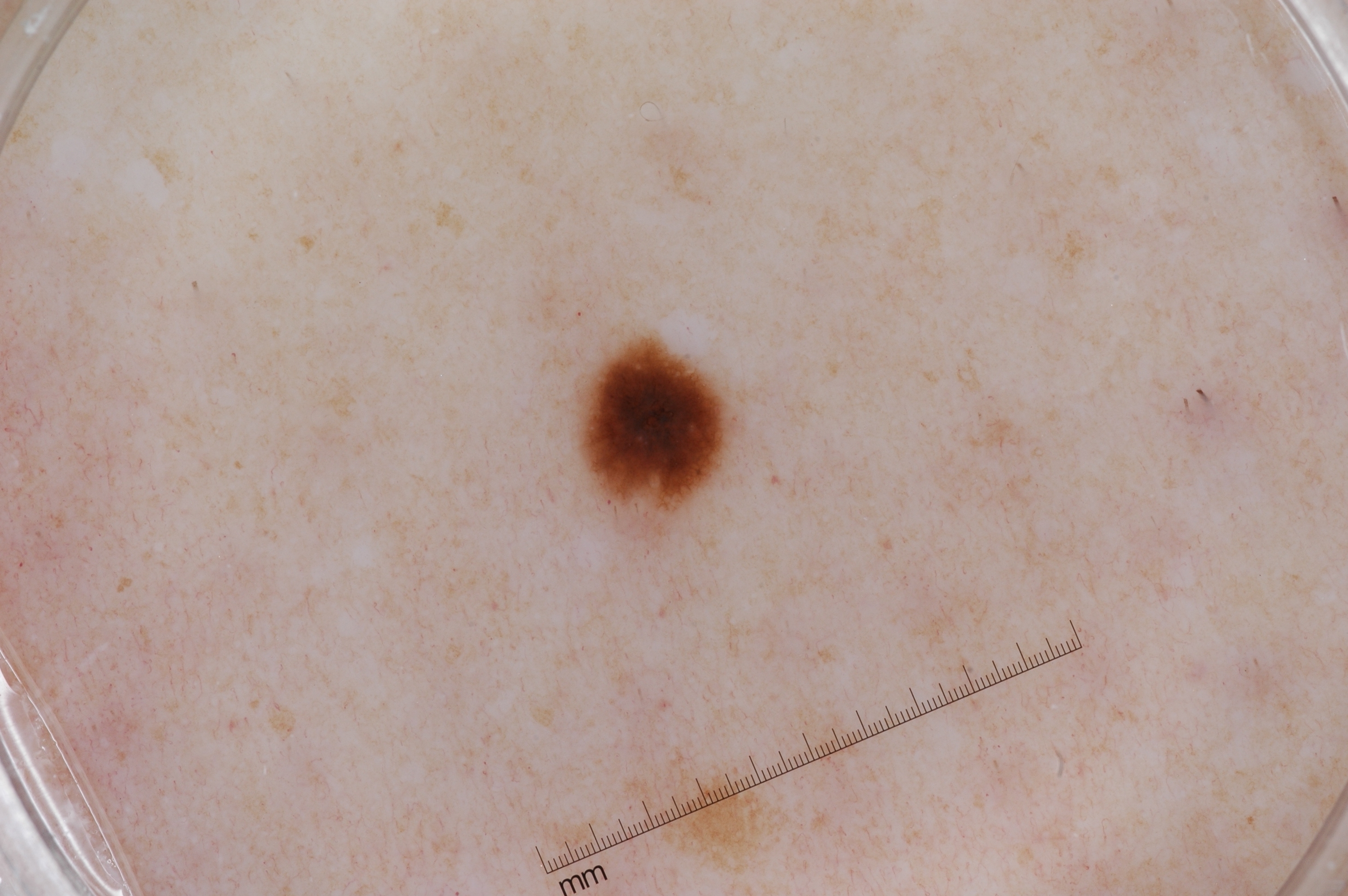A dermatoscopic image of a skin lesion. A small lesion within a wider field of skin. The dermoscopic pattern shows pigment network. In (x1, y1, x2, y2) order, the lesion's extent is 575, 336, 738, 541. Consistent with a melanocytic nevus.